A male subject 69 years of age. Recorded as Fitzpatrick phototype II. The chart records tobacco use, prior skin cancer (patient or family), and no prior malignancy (patient or family):
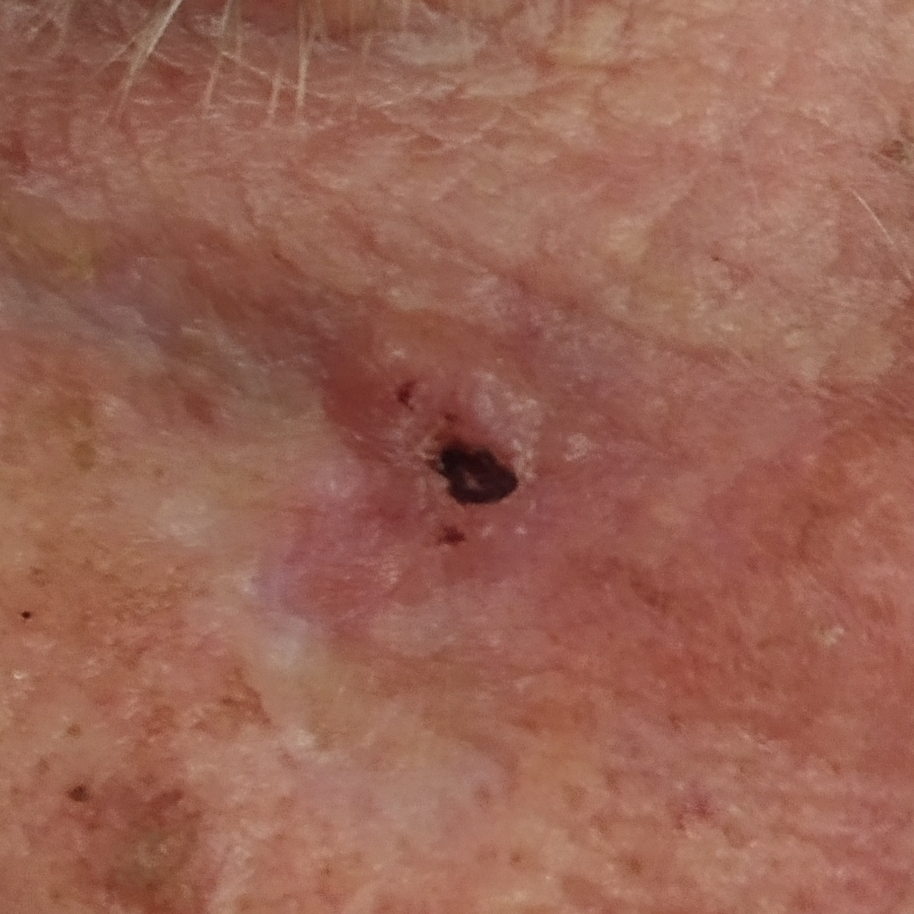Q: How large is the lesion?
A: 8x7 mm
Q: Any reported symptoms?
A: bleeding, elevation, itching / no pain
Q: What is the diagnosis?
A: basal cell carcinoma (biopsy-proven)